Dermoscopy of a skin lesion: 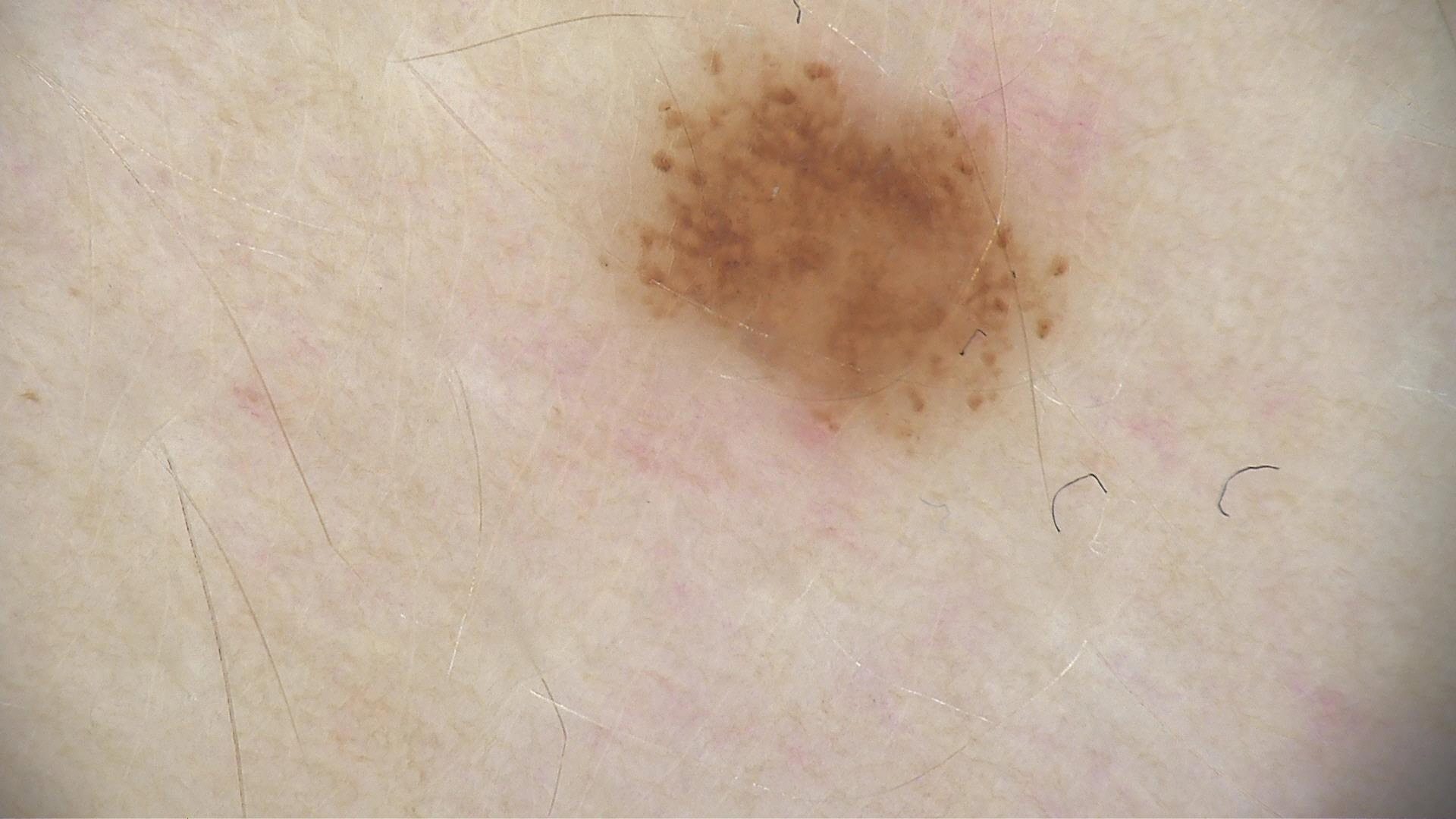Diagnosed as a dysplastic junctional nevus.